A smartphone photograph of a skin lesion · a subject in their early 40s: 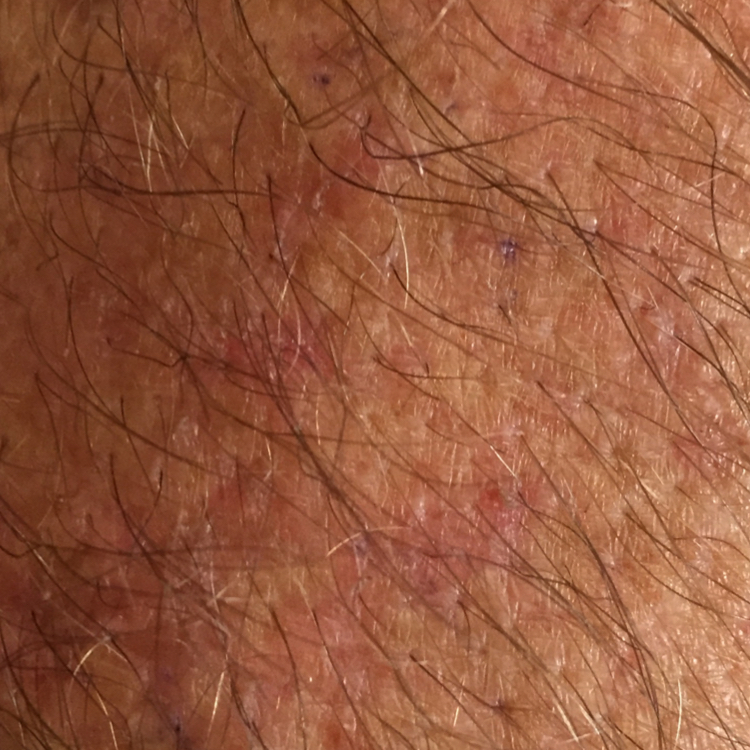| key | value |
|---|---|
| assessment | actinic keratosis (clinical consensus) |